Fitzpatrick III; lay reviewers estimated Monk skin tone scale 4 (US pool) or 2 (India pool). The photo was captured at an angle. The leg is involved. The patient described the issue as a rash. No associated systemic symptoms reported. The contributor reports the lesion is raised or bumpy and rough or flaky. The contributor reports the condition has been present for less than one week. The subject is a male aged 40–49: 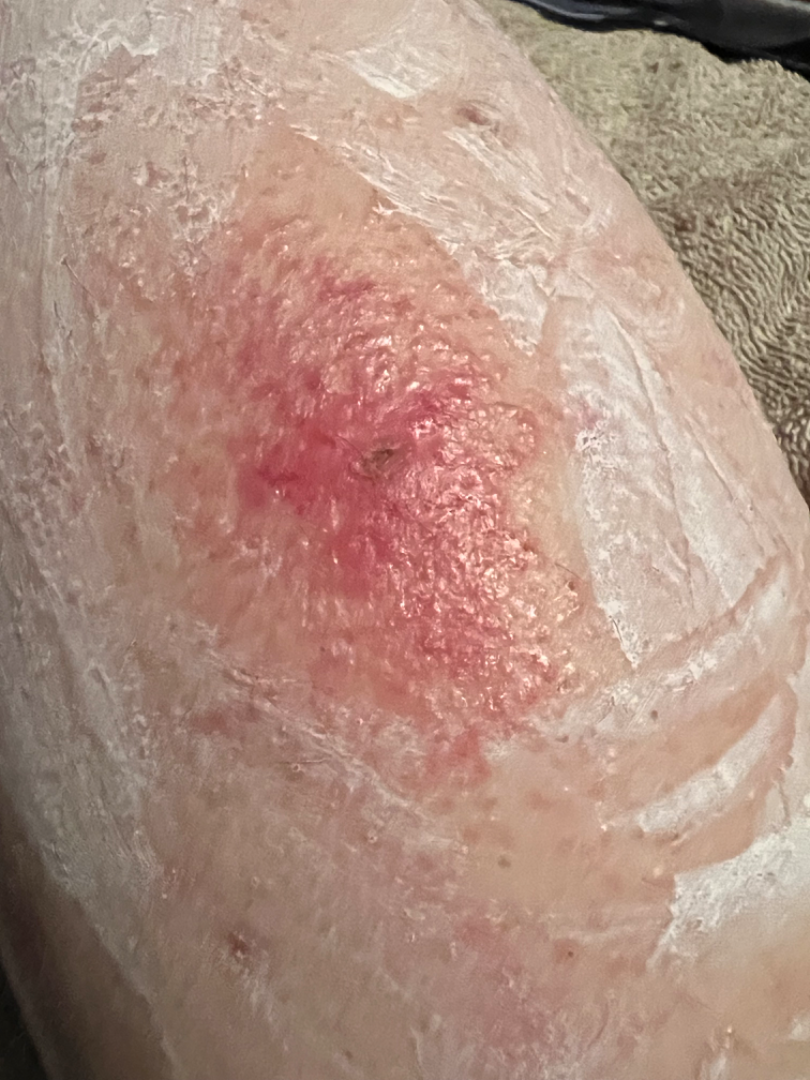diagnostic considerations: Leukocytoclastic Vasculitis (weight 1.00)